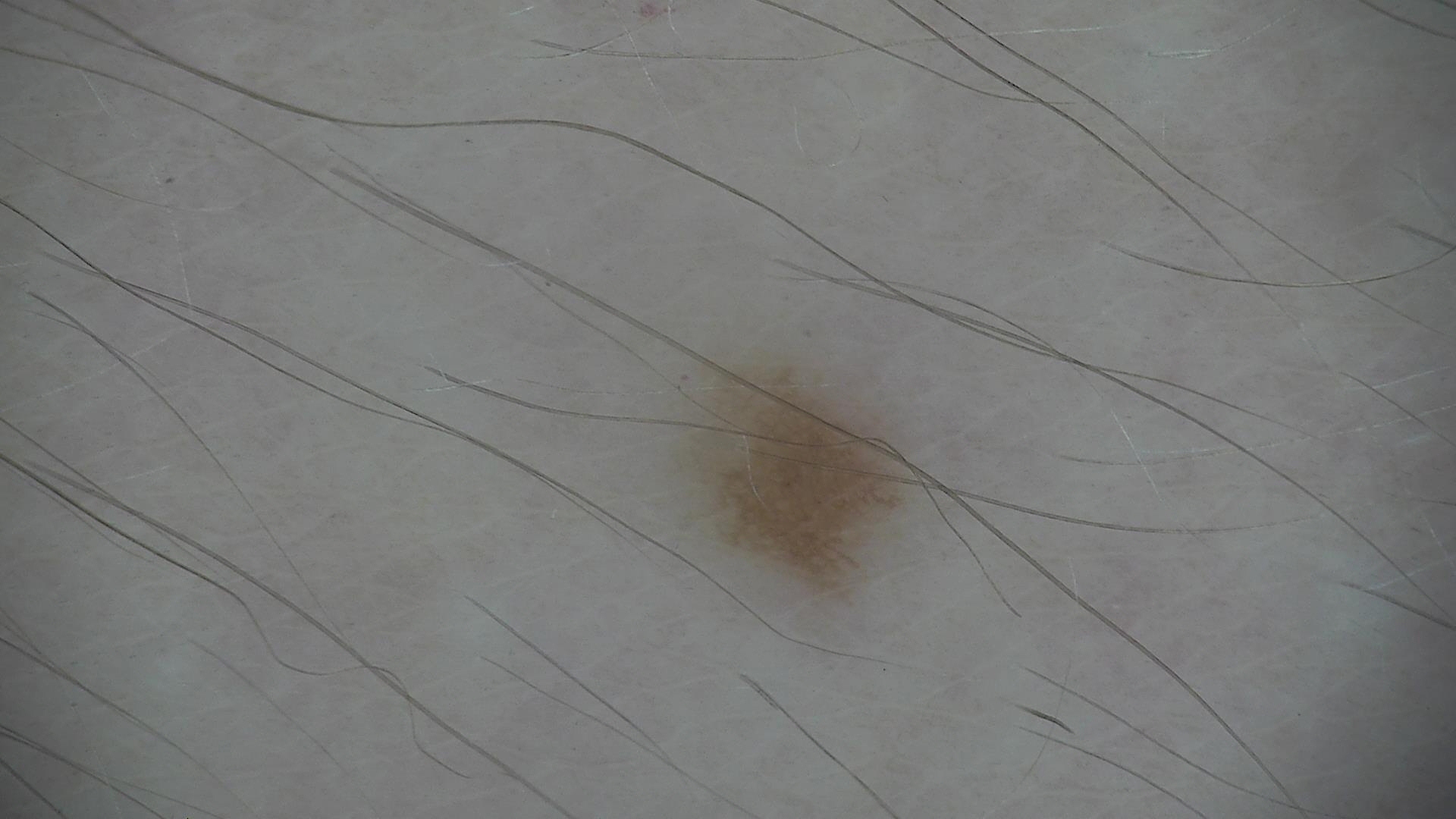Consistent with a benign lesion — a dysplastic junctional nevus.